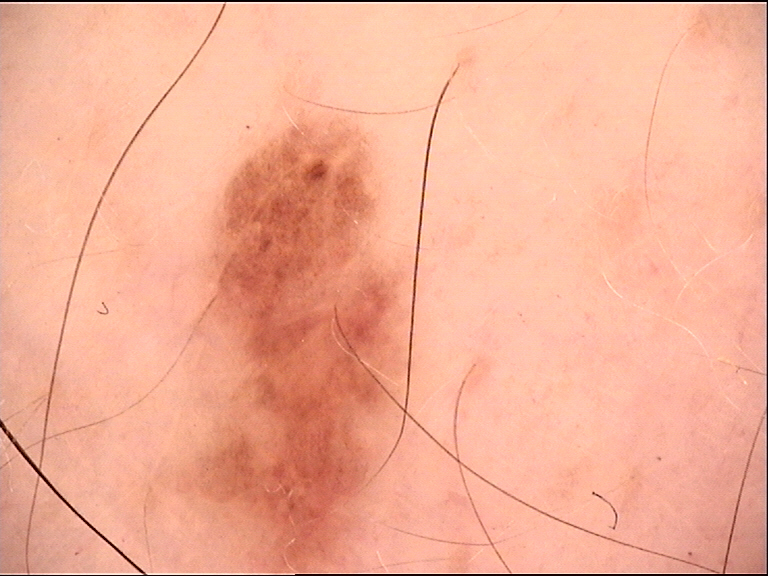Dermoscopy of a skin lesion. Consistent with a dysplastic junctional nevus.